The patient indicates the condition has been present for one to four weeks, texture is reported as rough or flaky, the arm is involved, close-up view, the lesion is associated with itching: 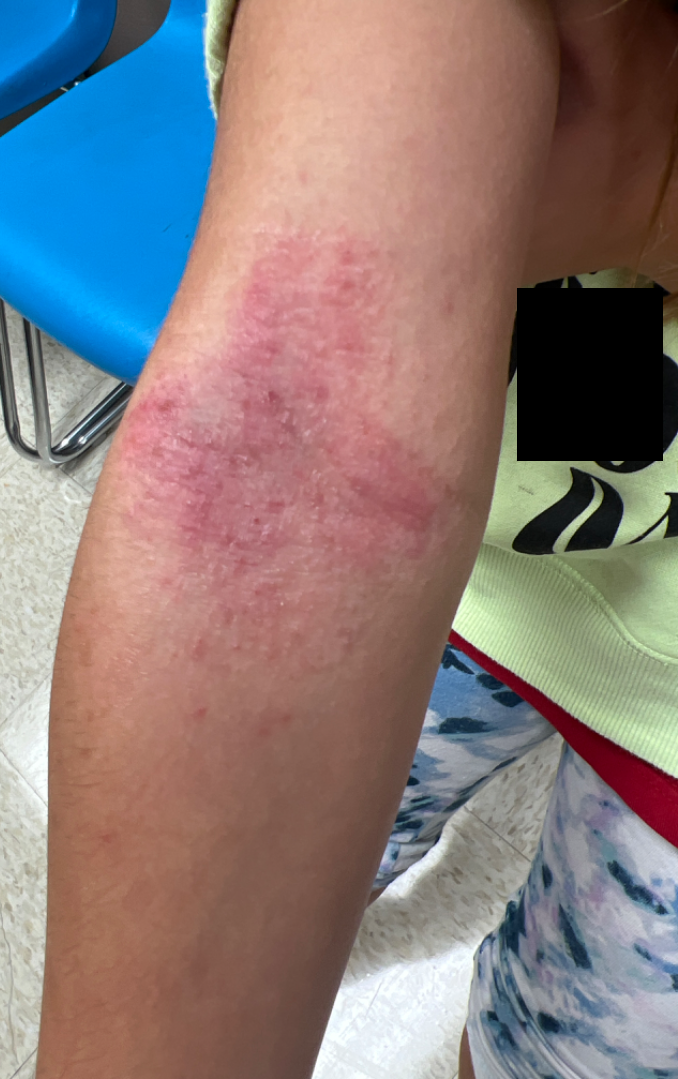The reviewer's impression was Eczema.